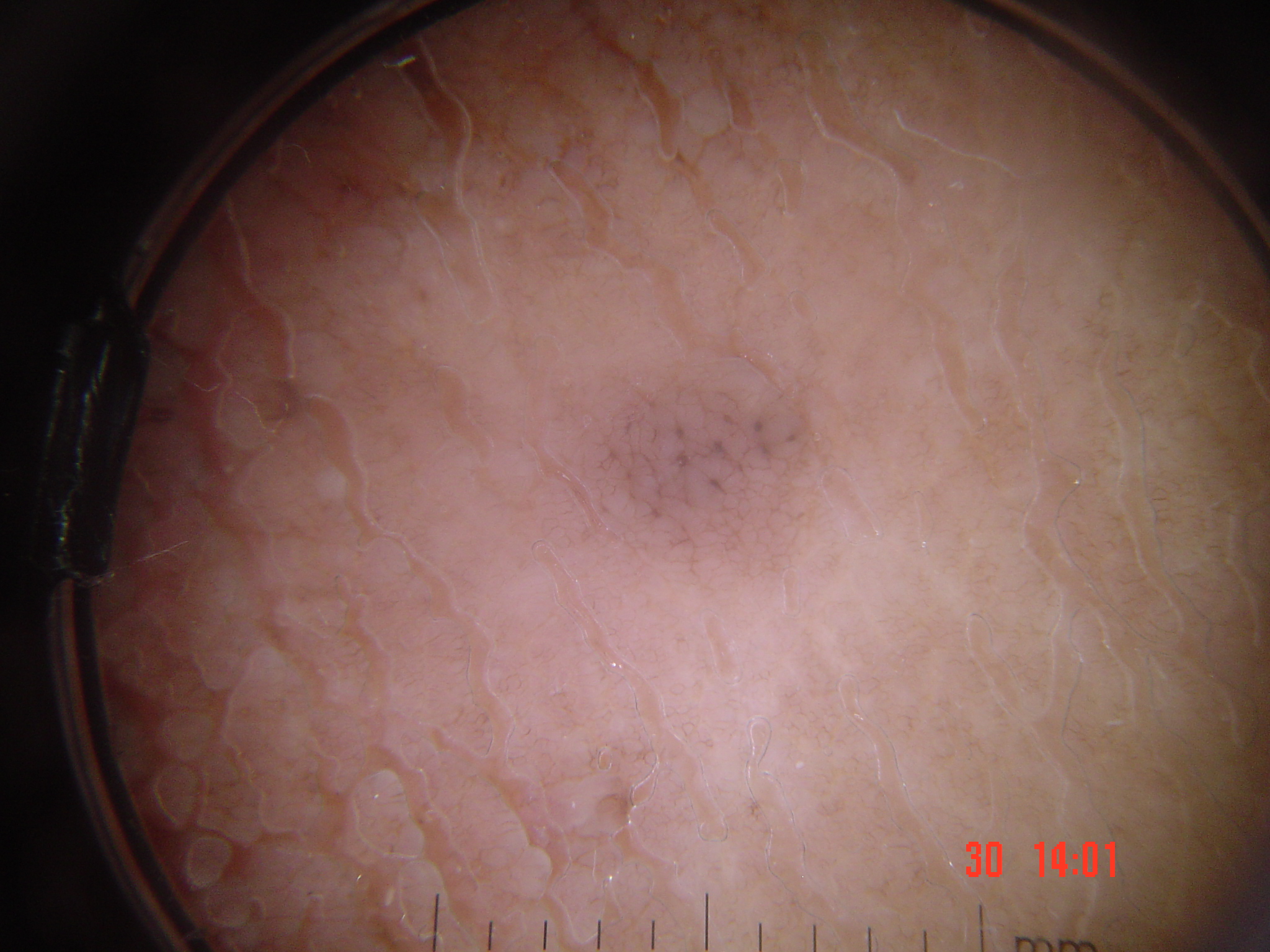A skin lesion imaged with a dermatoscope. The morphology is that of a keratinocytic lesion. Consistent with a benign lesion — a seborrheic keratosis.